Located on the leg, an image taken at an angle, the patient is female: 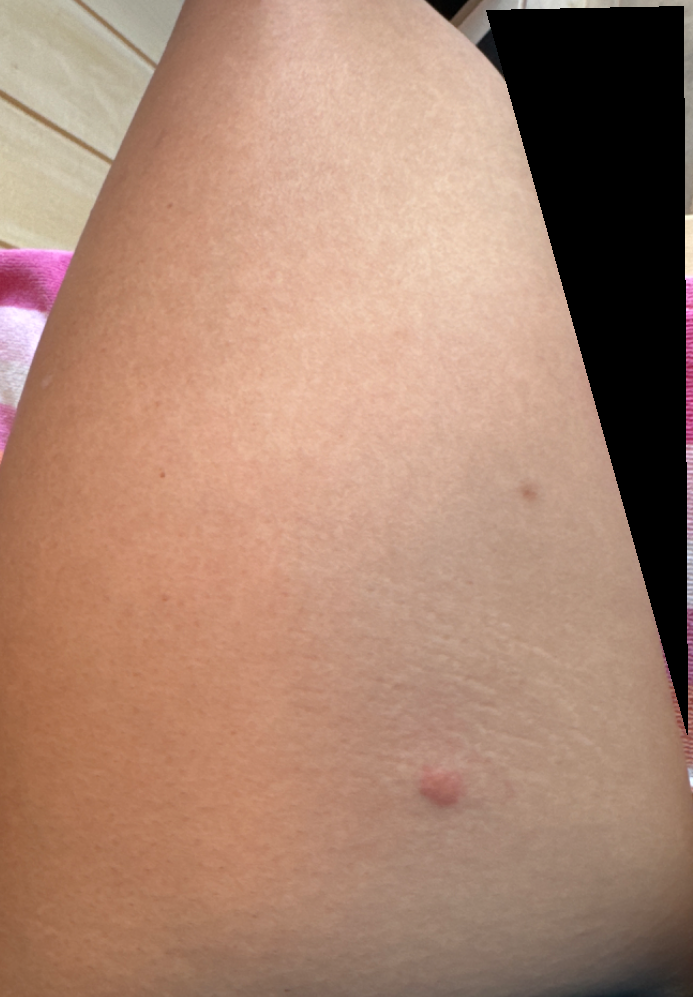The reviewer was unable to grade this case for skin condition.
Reported duration is less than one week.
The patient indicates the lesion is raised or bumpy.
The patient considered this a growth or mole.
The patient indicates bothersome appearance and enlargement.